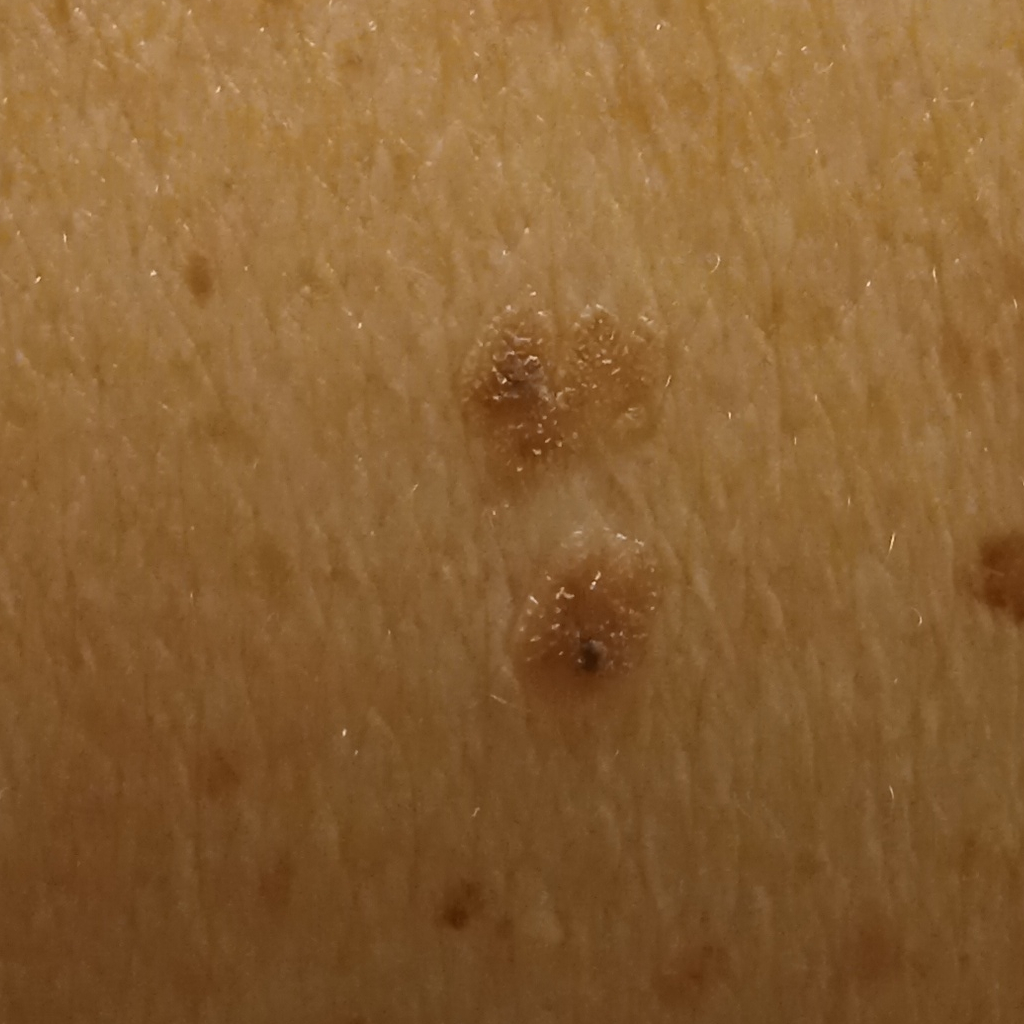The patient reports a personal history of skin cancer, immunosuppression, and a personal history of cancer.
The patient says their skin reddens painfully with sun exposure.
The patient describes having a moderate number of moles.
Collected as part of a research study, without a referral diagnosis.
A clinical close-up of a skin lesion.
Located on the back.
The lesion measures approximately 6.2 mm.
The lesion was assessed as a seborrheic keratosis.